A dermatoscopic image of a skin lesion: 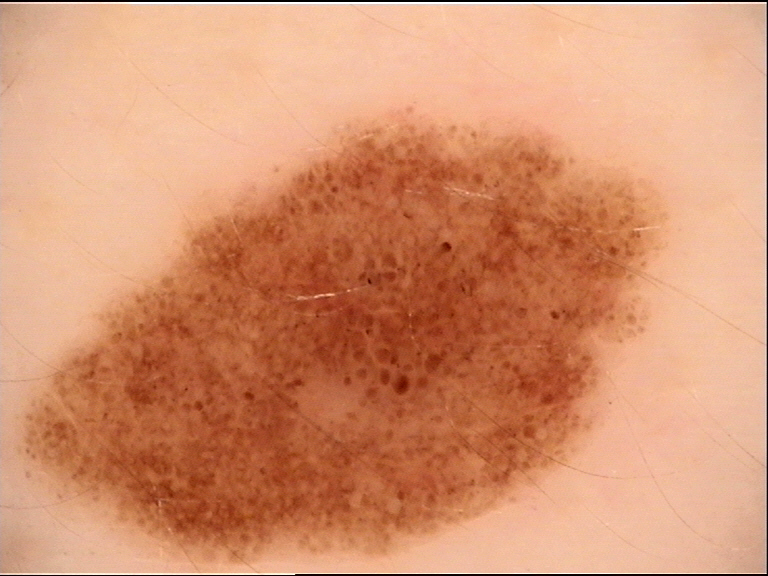Impression:
The diagnostic label was a benign lesion — a dysplastic junctional nevus.